Dermoscopy of a skin lesion.
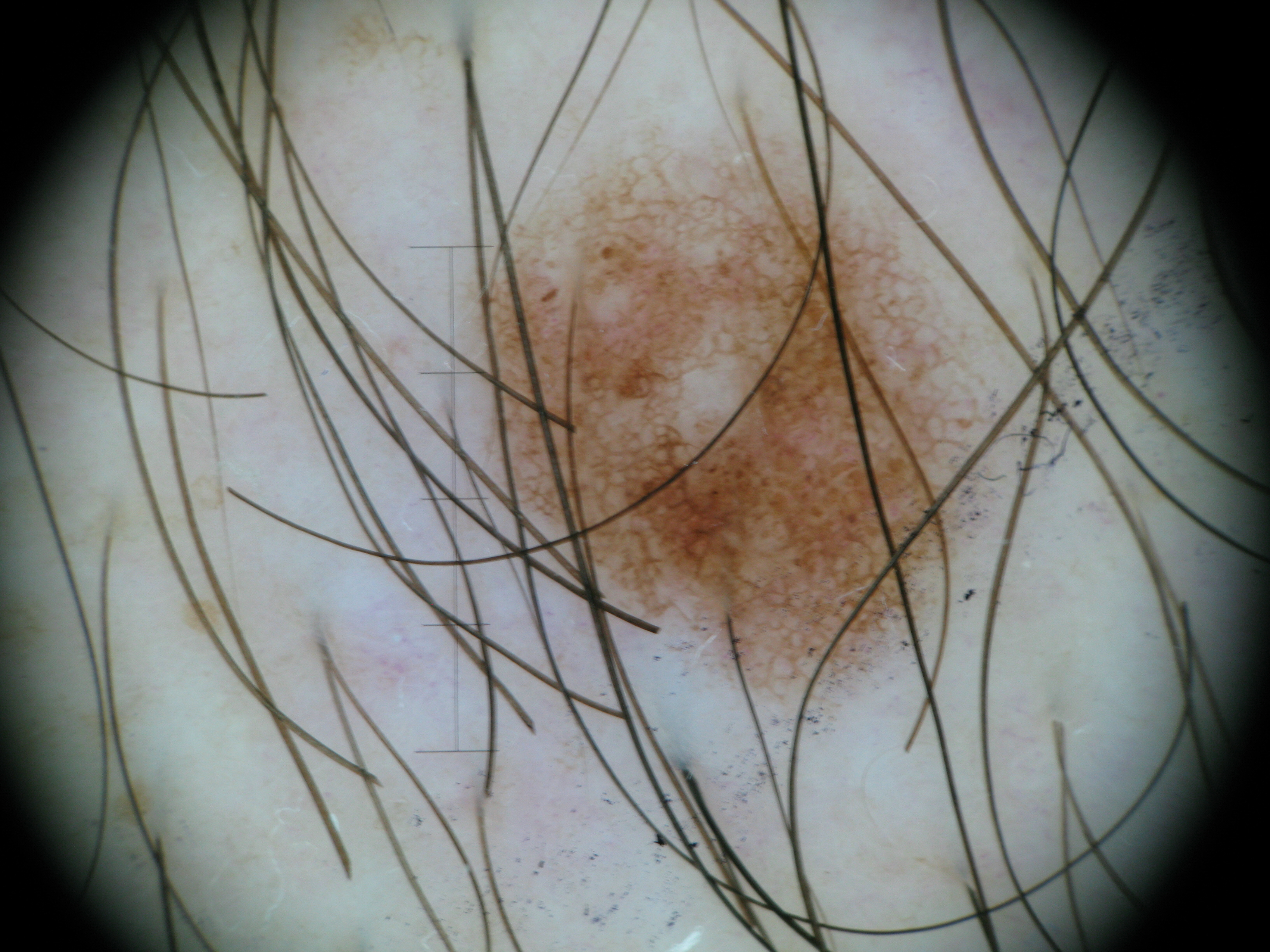Findings:
• class: dysplastic junctional nevus (expert consensus)